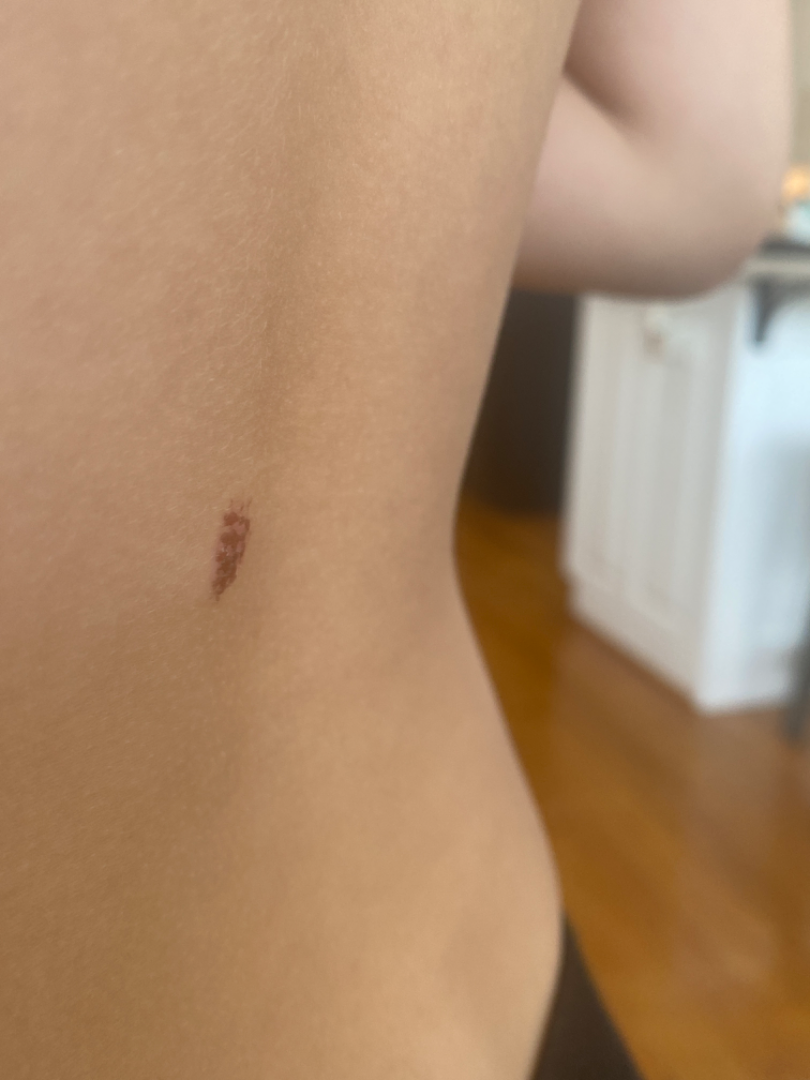No differential diagnosis could be assigned on photographic review.